Referred with a clinical suspicion of melanoma. A male subject aged 78. The patient reports a personal history of cancer and no personal history of skin cancer. A clinical photograph showing a skin lesion. Few moles overall by the patient's own estimate: 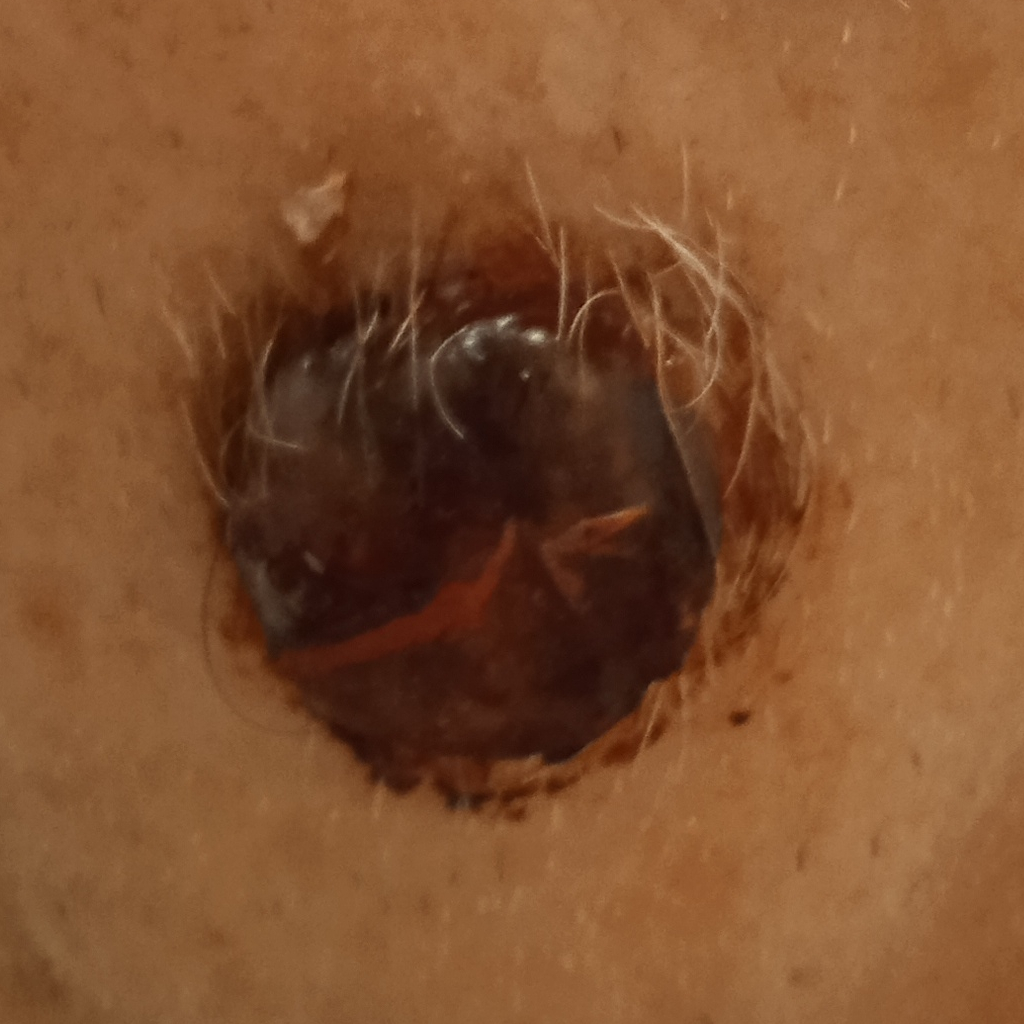The lesion involves the face.
The lesion measures approximately 19.9 mm.
Confirmed on histopathology as a melanoma, following excision.